Close-up view, the contributor is a female aged 40–49, the lesion involves the back of the torso and front of the torso — 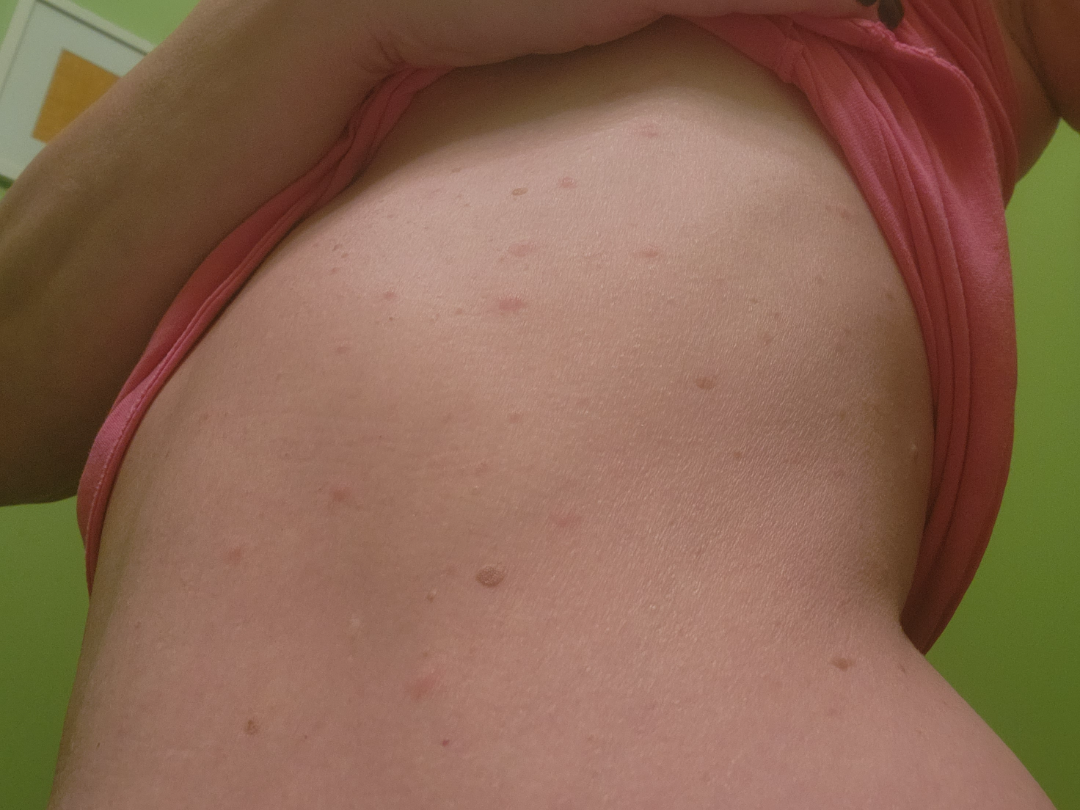Self-categorized by the patient as a rash. The lesion is associated with itching and bothersome appearance. The patient notes the condition has been present for about one day. Texture is reported as raised or bumpy. Skin tone: FST III. On remote dermatologist review, most likely Pityriasis rosea.